A subject 84 years old · a clinical photograph showing a skin lesion.
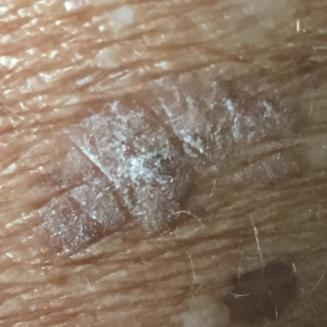<record>
<lesion_location>an arm</lesion_location>
<symptoms>
<present>elevation, itching</present>
</symptoms>
<diagnosis>
<name>seborrheic keratosis</name>
<code>SEK</code>
<malignancy>benign</malignancy>
<confirmation>clinical consensus</confirmation>
</diagnosis>
</record>